A dermoscopic close-up of a skin lesion: 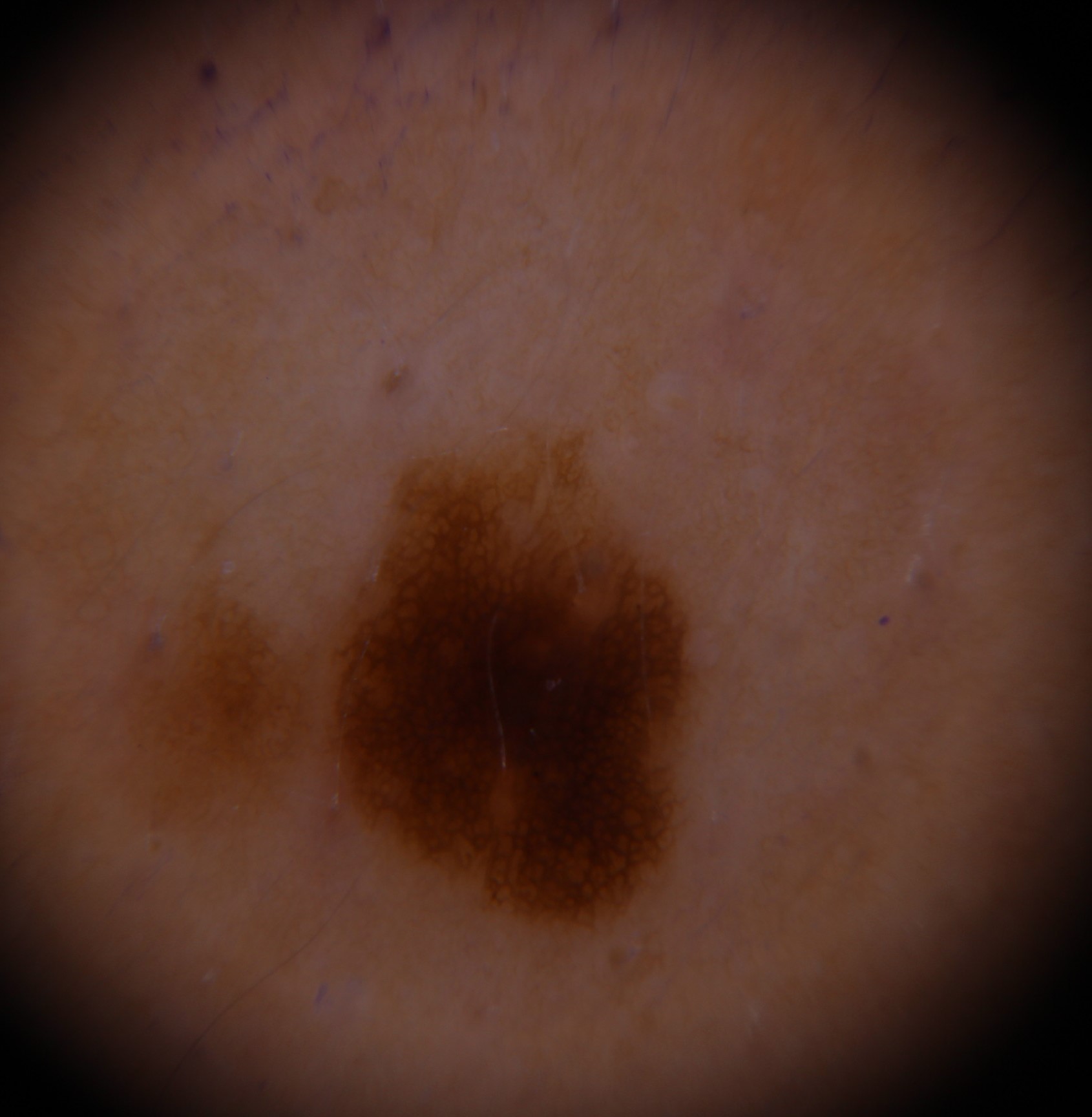Consistent with a benign lesion — a dysplastic junctional nevus.